A dermatoscopic image of a skin lesion.
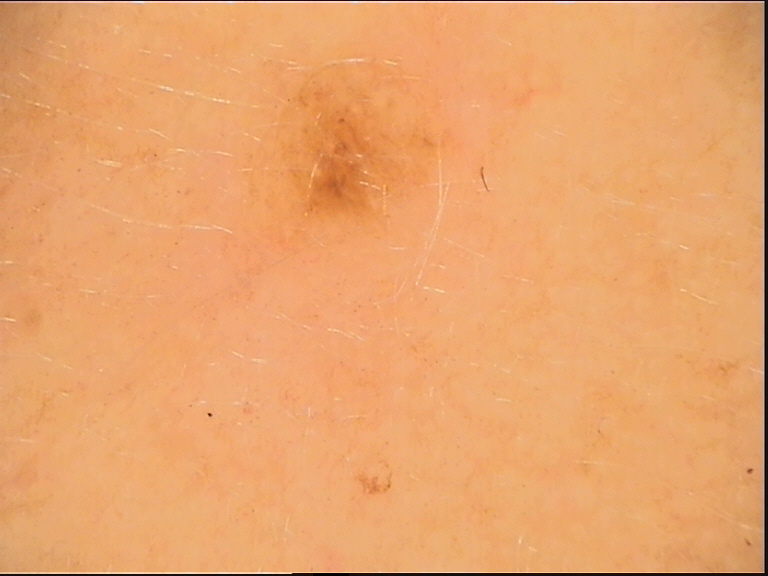Consistent with a dysplastic junctional nevus.